A male subject 45 years of age; a clinical photograph showing a skin lesion:
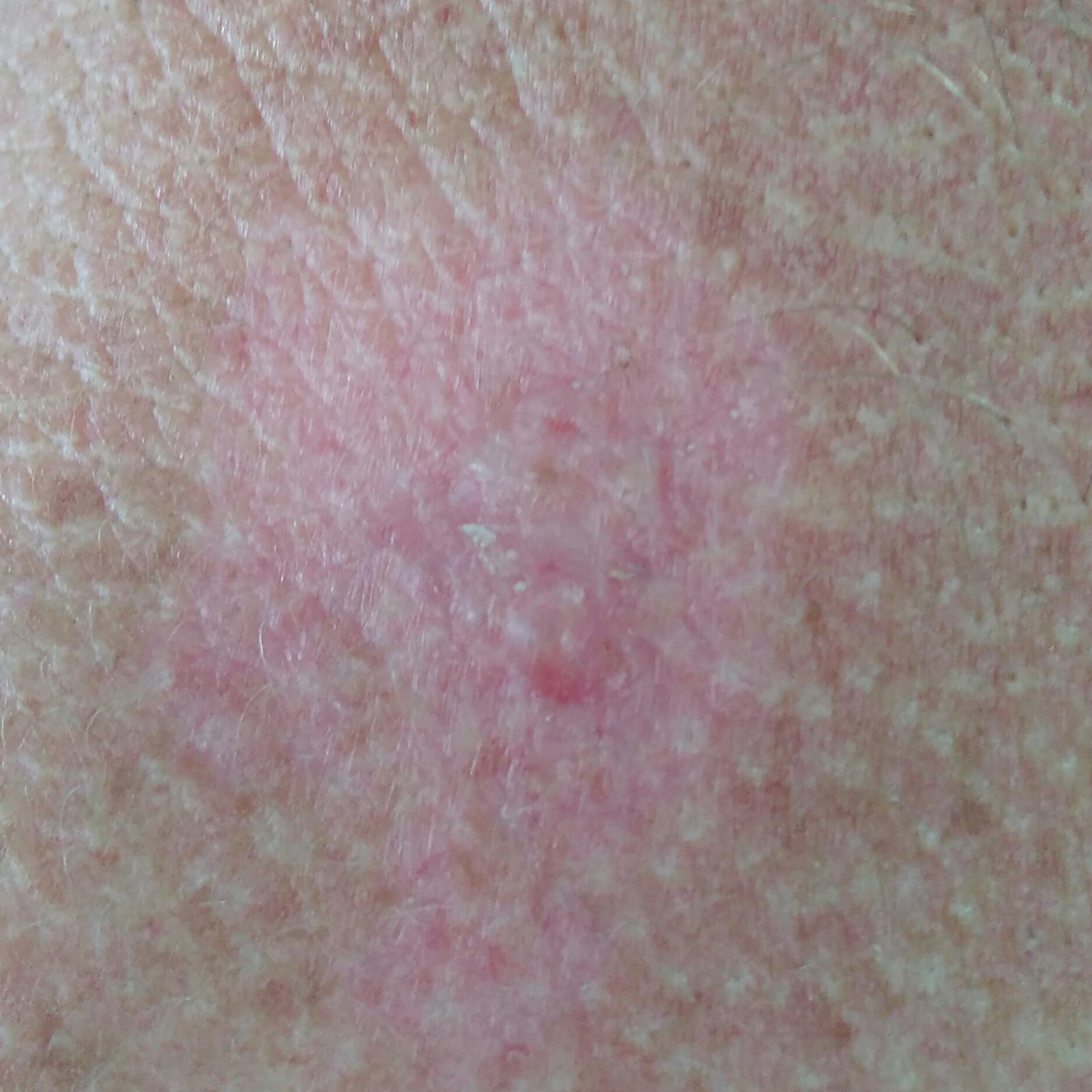symptoms: no elevation, no pain; diagnostic label: basal cell carcinoma (biopsy-proven).